This is a close-up image:
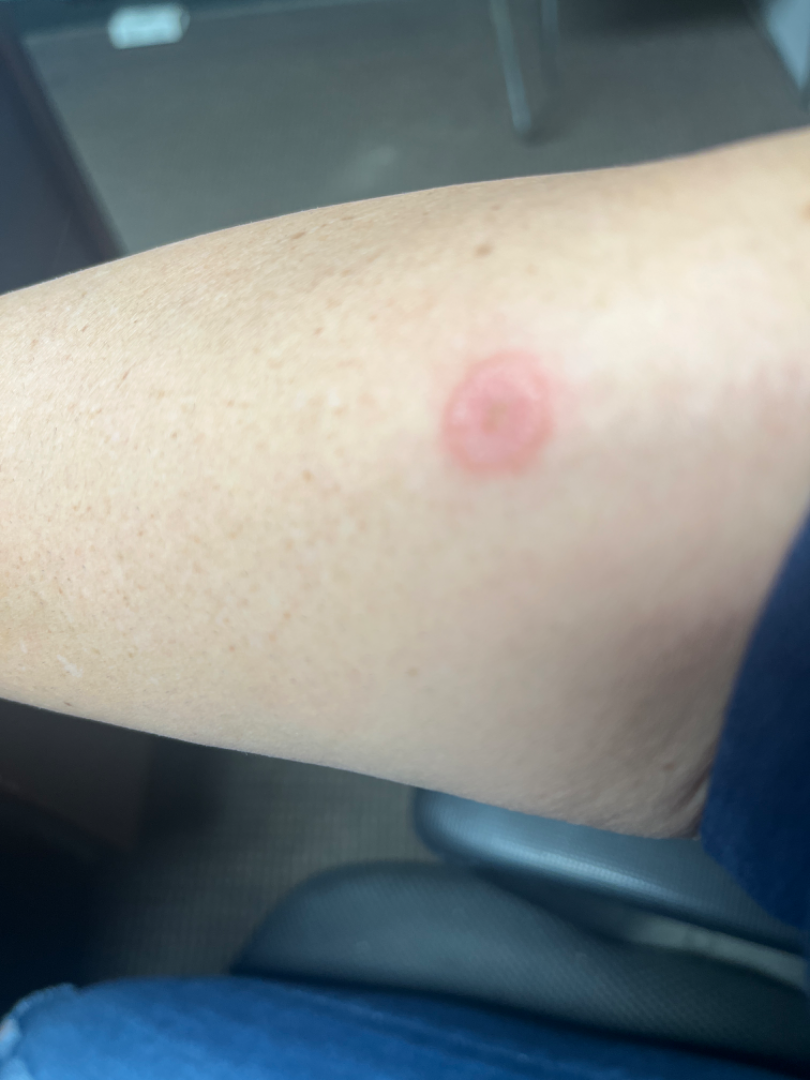Diagnostic features were not clearly distinguishable in this photograph.
Skin tone: Fitzpatrick phototype III.
Texture is reported as rough or flaky and raised or bumpy.